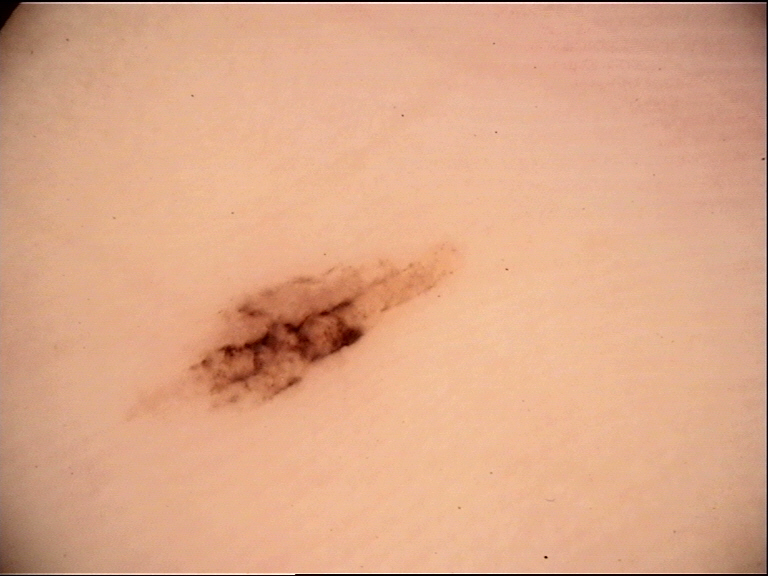Q: What is the diagnosis?
A: acral dysplastic junctional nevus (expert consensus)